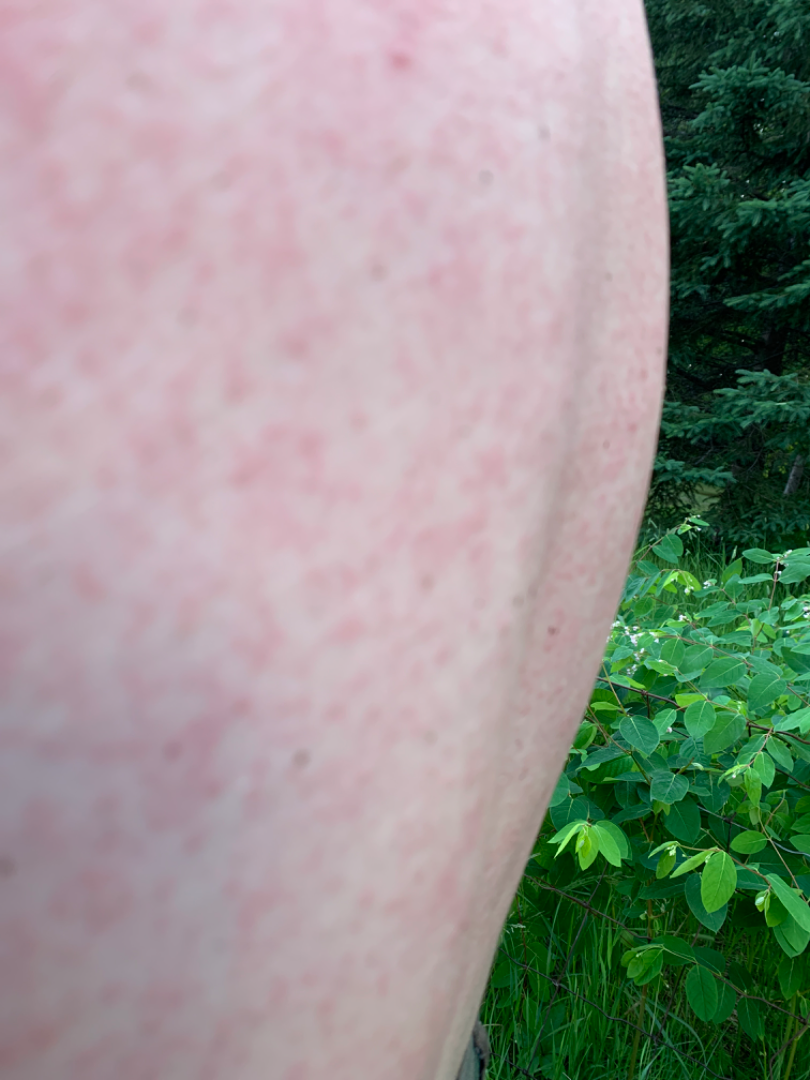The case was indeterminate on photographic review.
An image taken at an angle.
Skin tone: Fitzpatrick II; lay reviewers estimated a MST of 2.
The patient considered this a rash.
Reported duration is about one day.
Located on the back of the torso.
Reported lesion symptoms include pain.
The lesion is described as raised or bumpy.